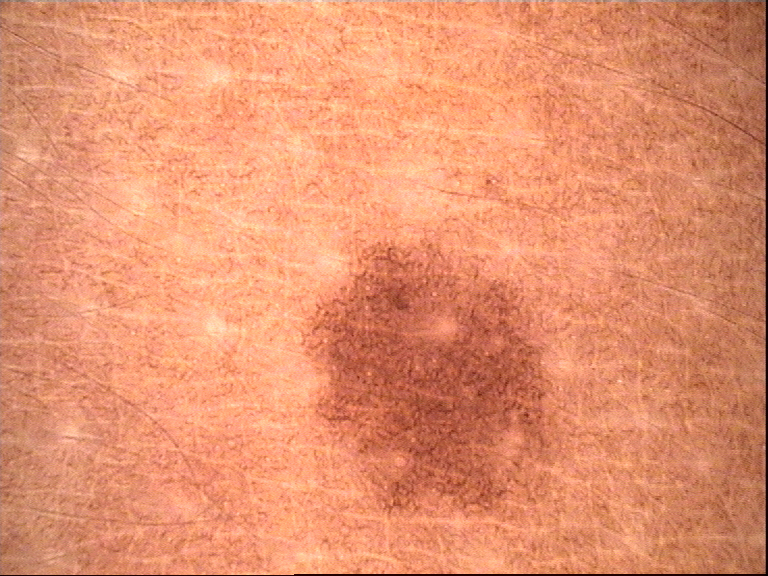Case:
* modality: dermatoscopy
* label: dysplastic junctional nevus (expert consensus)